Dermoscopy of a skin lesion: 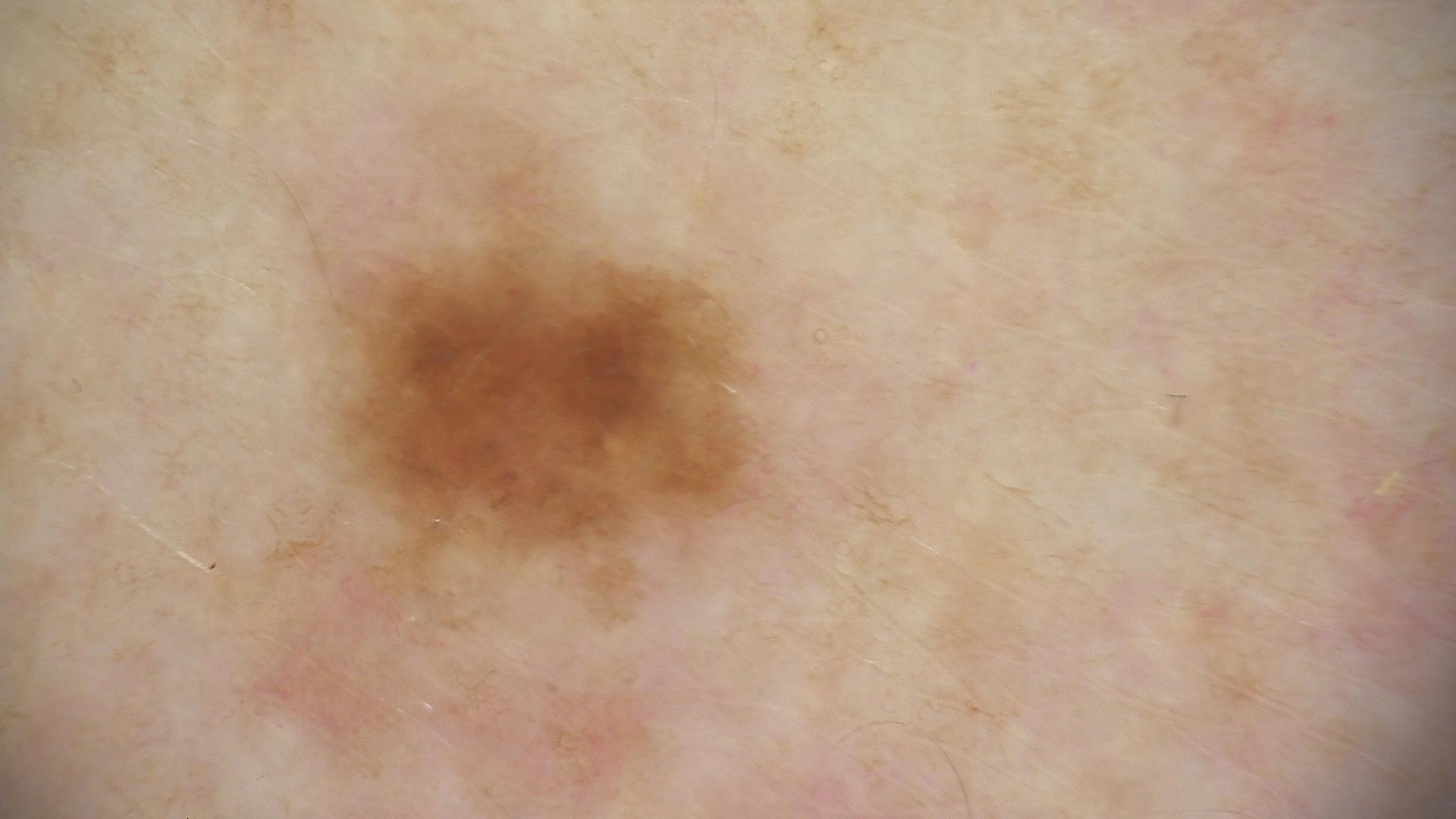Findings:
– class: dysplastic junctional nevus (expert consensus)